A dermoscopic view of a skin lesion. A male subject, aged around 85 or older: 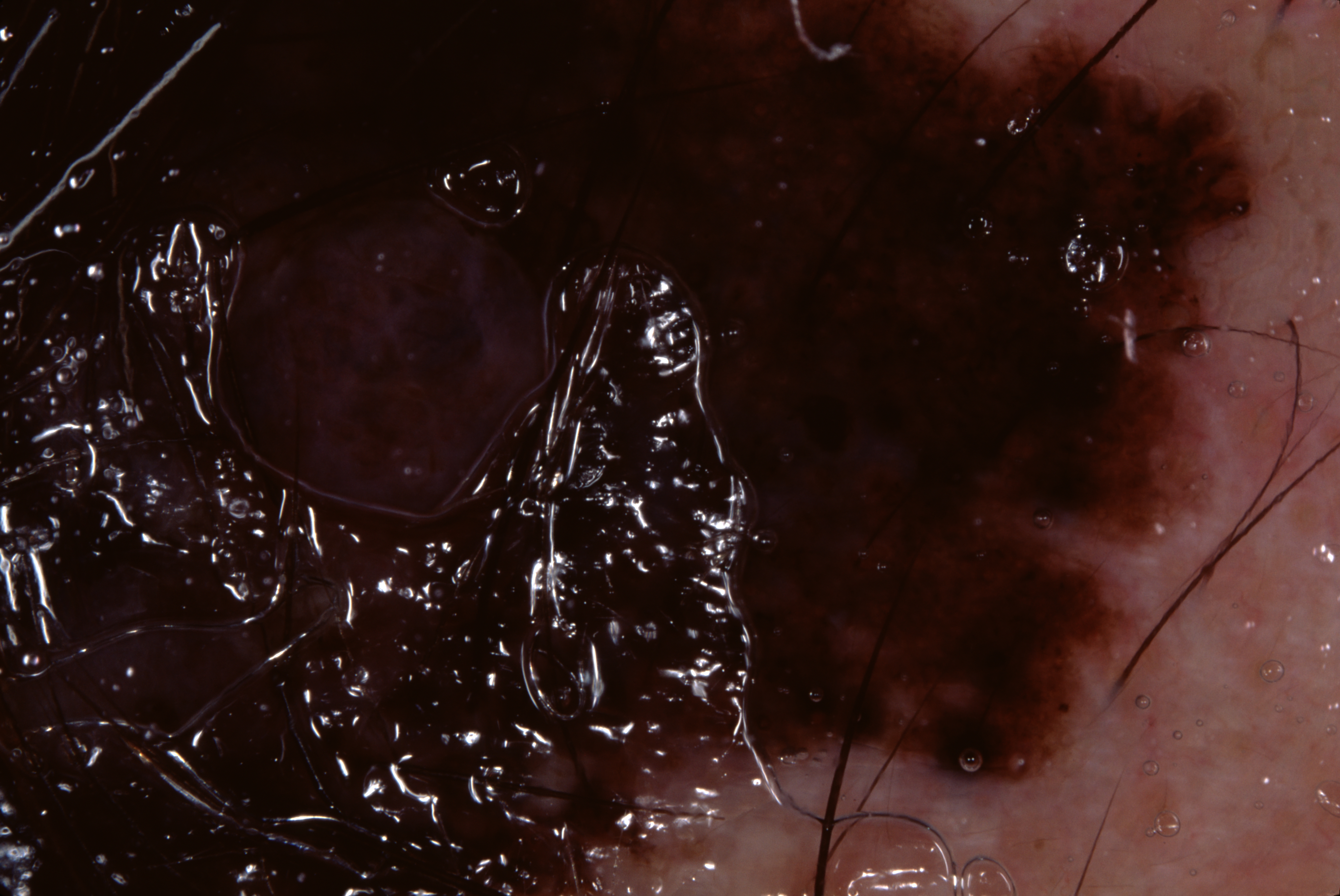Dermoscopically, the lesion shows streaks.
The lesion extends across almost the whole field of view.
The biopsy diagnosis was a melanoma.